This image was taken at an angle. The subject is a male aged 18–29. Self-categorized by the patient as a rash. The leg is involved. The condition has been present for less than one week — 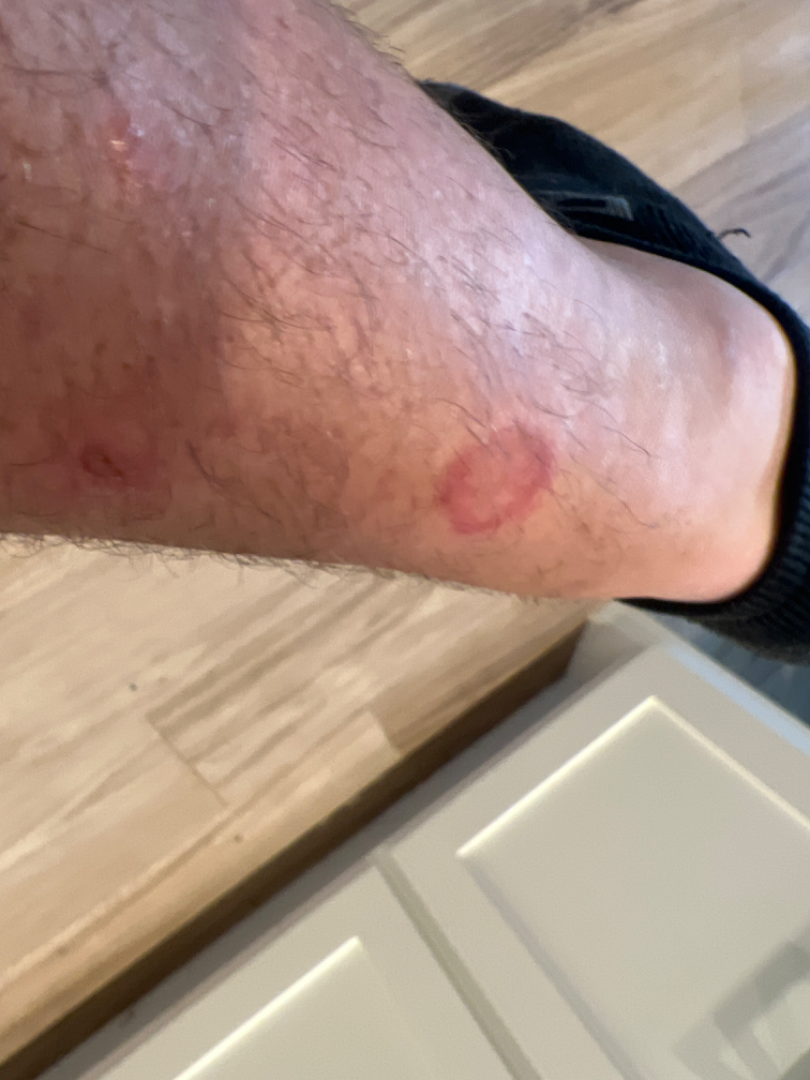Case summary:
• assessment: indeterminate from the photograph